Present for one to four weeks; the lesion is described as rough or flaky and raised or bumpy; reported lesion symptoms include enlargement and itching; no associated systemic symptoms reported; self-categorized by the patient as a rash; the subject is a female aged 40–49; Fitzpatrick phototype I; the photograph was taken at an angle — 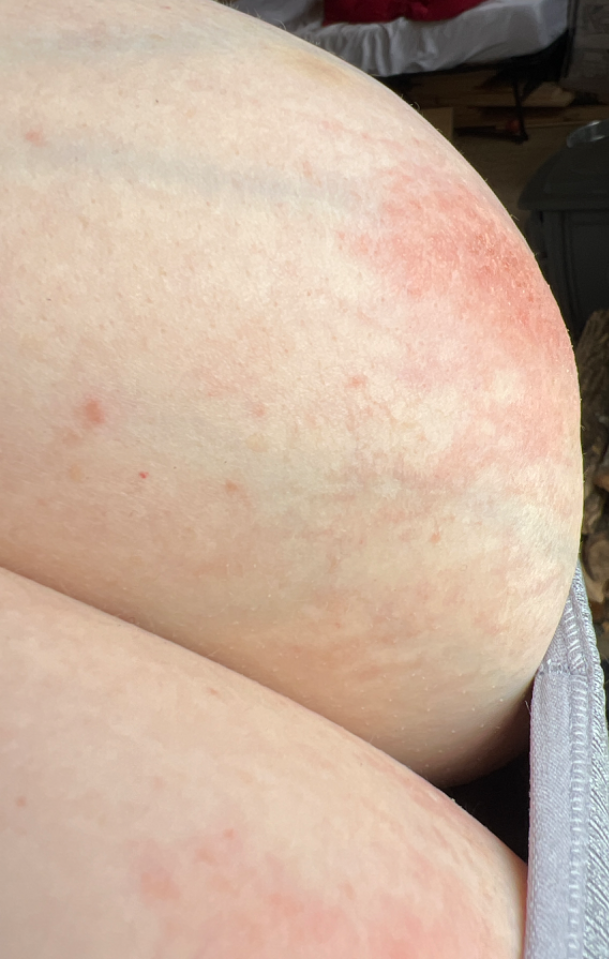clinical impression: the differential includes Eczema and Allergic Contact Dermatitis, with no clear leading consideration; less probable is Psoriasis.